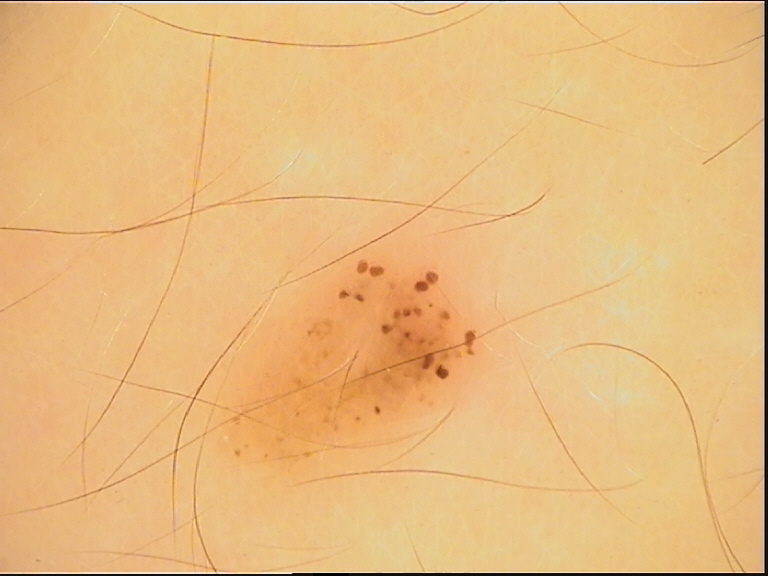Dermoscopy of a skin lesion. The diagnosis was a dysplastic junctional nevus.